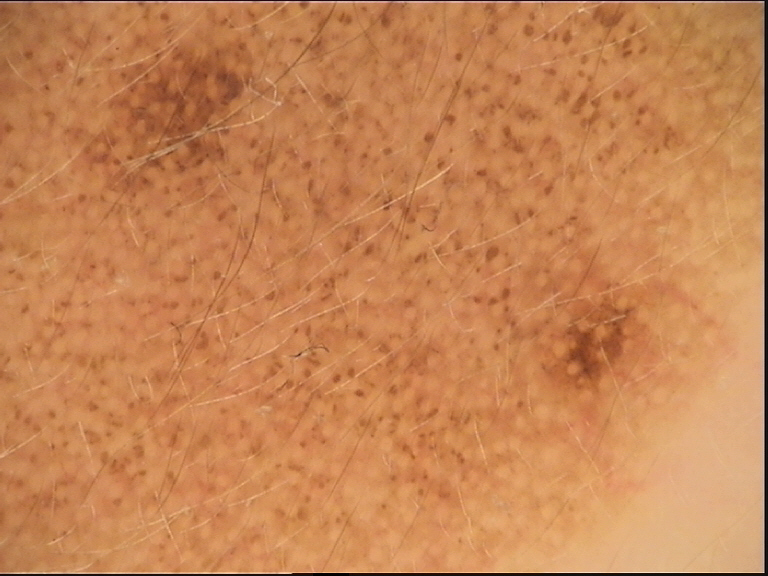Classified as a banal lesion — a congenital junctional nevus.